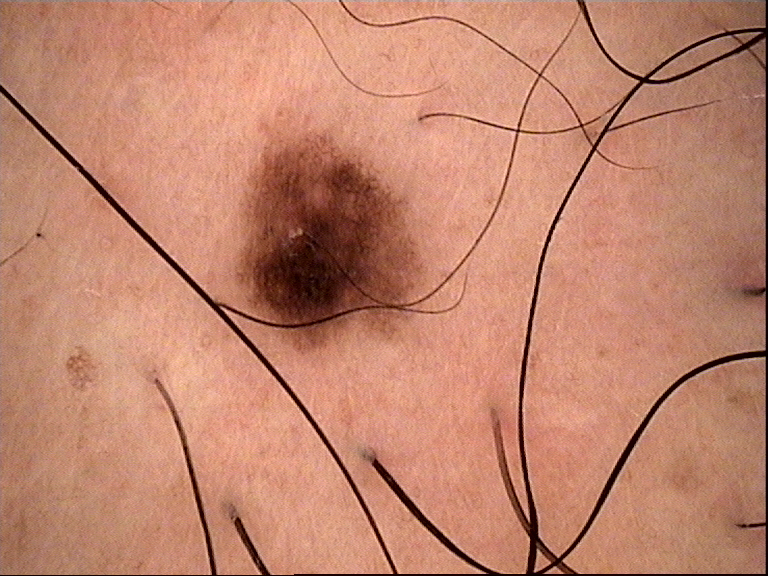Consistent with a dysplastic junctional nevus.